An image taken at a distance. The lesion involves the back of the torso: 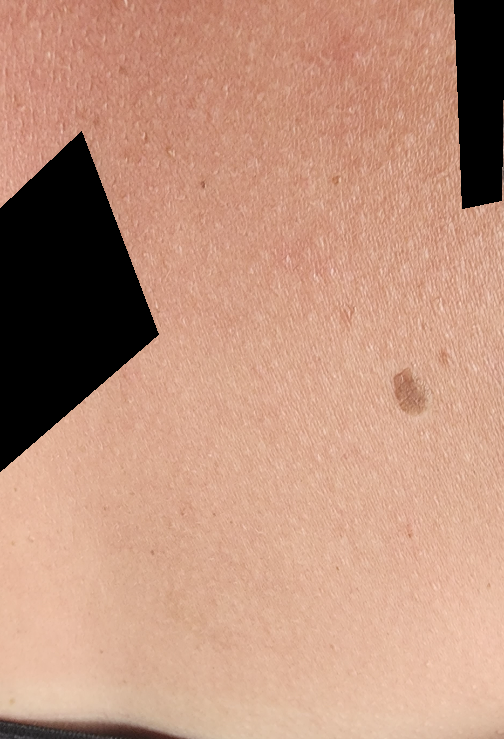dermatologist impression = SK/ISK (weight 0.55); Melanocytic Nevus (weight 0.27); Actinic Keratosis (weight 0.18).